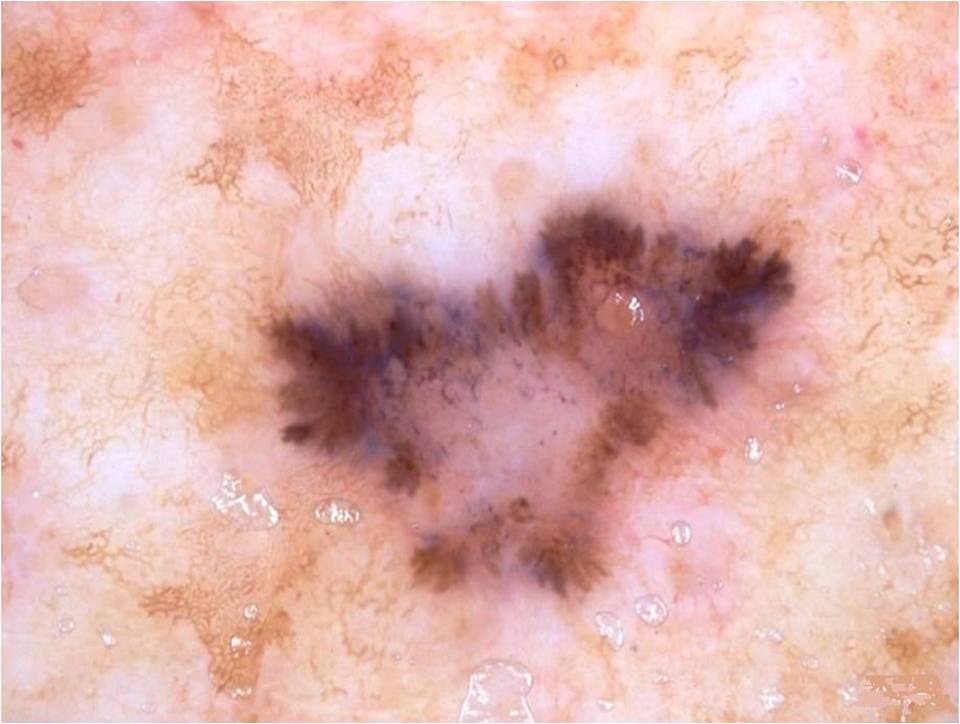A dermoscopic view of a skin lesion. As (left, top, right, bottom), the lesion occupies the region [246,190,812,610]. The lesion covers approximately 23% of the dermoscopic field. Dermoscopic review identifies globules and streaks, with no milia-like cysts, pigment network, or negative network. Histopathologically confirmed as a melanoma, a malignant lesion.